Dermoscopy of a skin lesion. A female subject, aged 68 to 72.
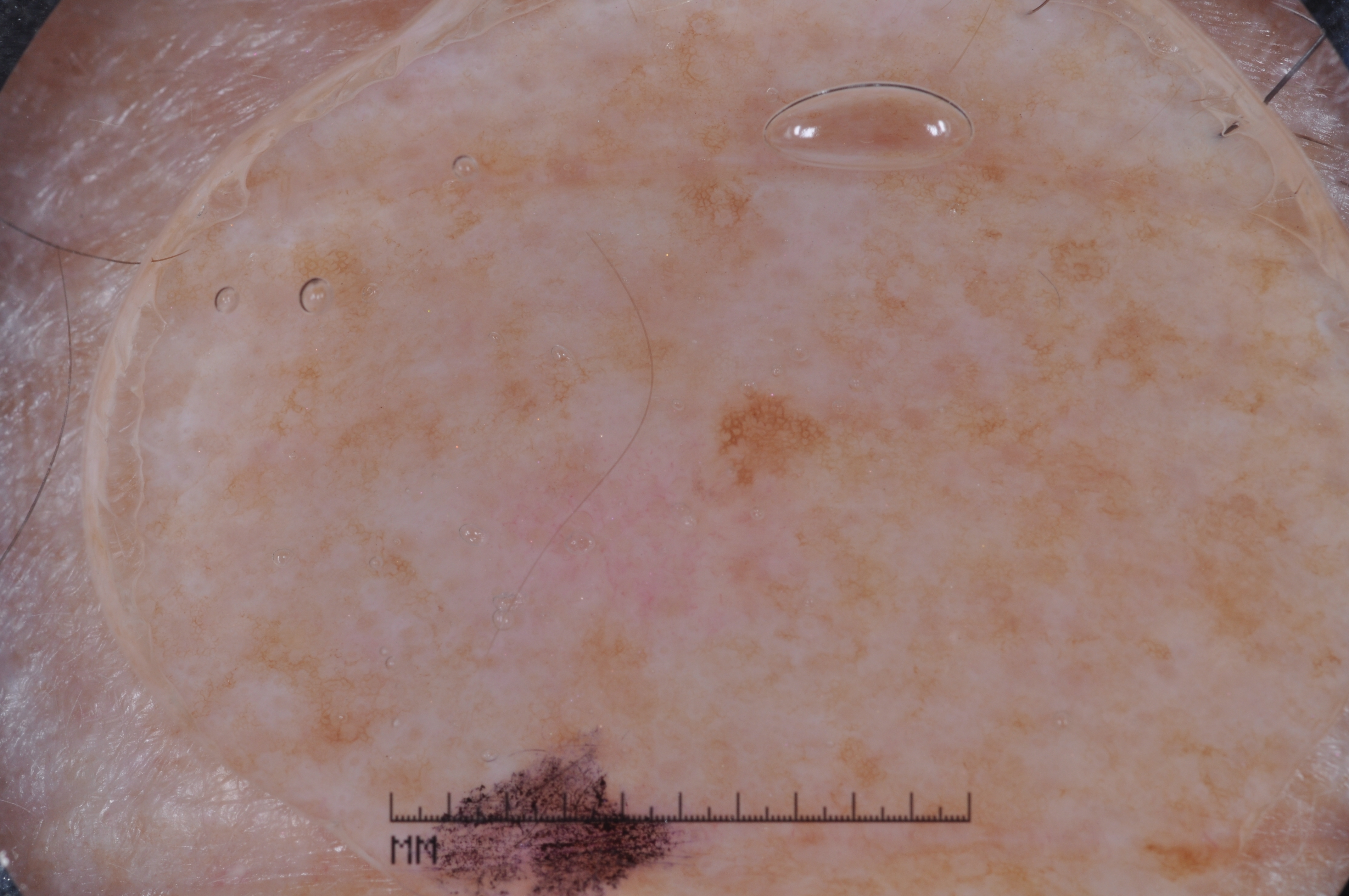dermoscopic pattern: pigment network
lesion bbox: box(475, 423, 756, 642)
diagnosis: a melanoma